A dermoscopic image of a skin lesion: 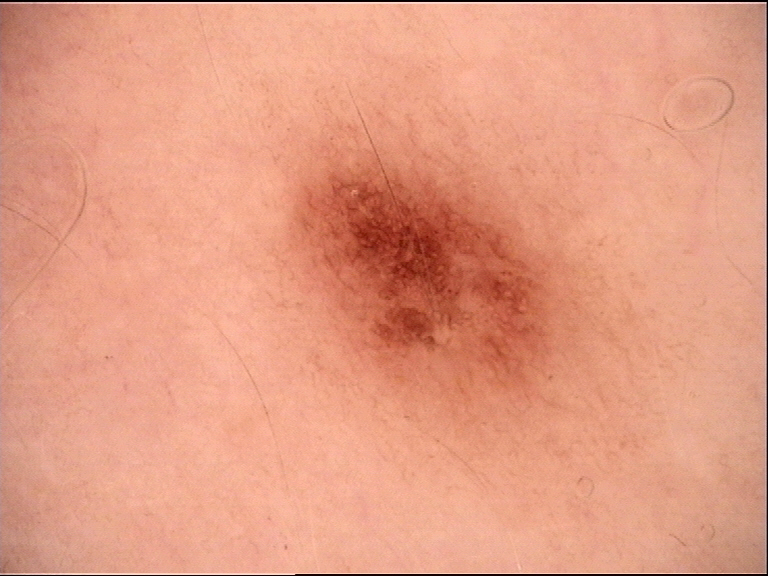Case:
– diagnosis — dysplastic junctional nevus (expert consensus)